Located on the head or neck, close-up view.
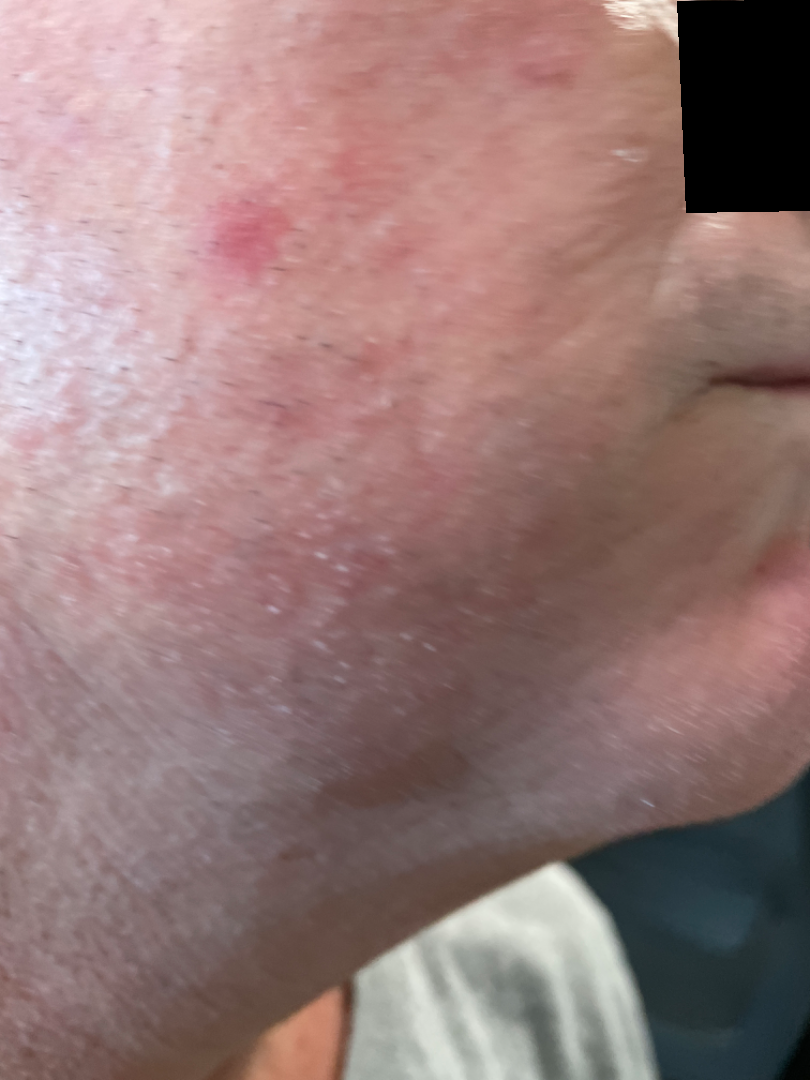assessment: unable to determine
skin tone: Fitzpatrick skin type II
reported symptoms: itching
described texture: flat
onset: one to three months